A macroscopic clinical photograph of a skin lesion. Acquired for a research image collection, with no referral diagnosis. The patient describes having a moderate number of moles. The patient says their skin reddens painfully with sun exposure. A female patient aged 35: 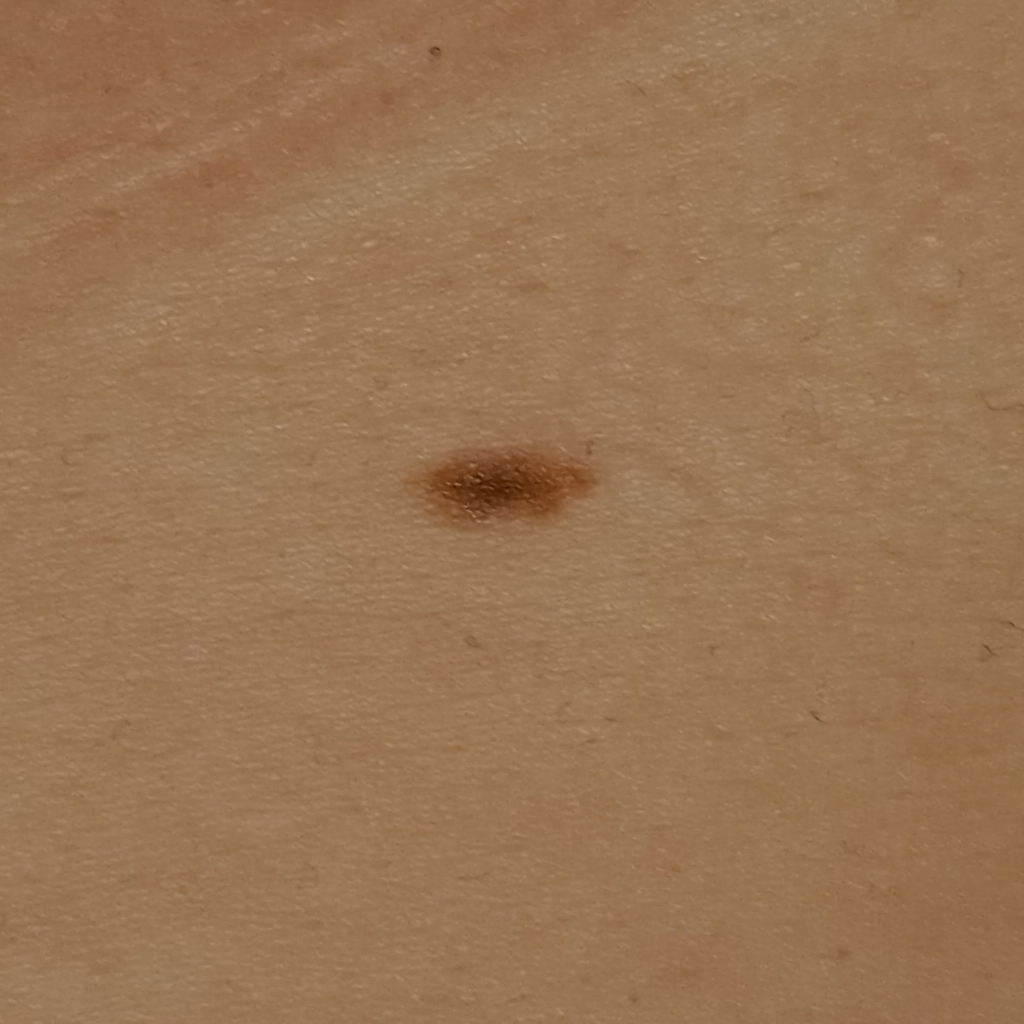{"lesion_location": "the torso", "lesion_size": {"diameter_mm": 6.3}, "diagnosis": {"name": "melanocytic nevus", "malignancy": "benign"}}